A close-up photograph. The leg is involved:
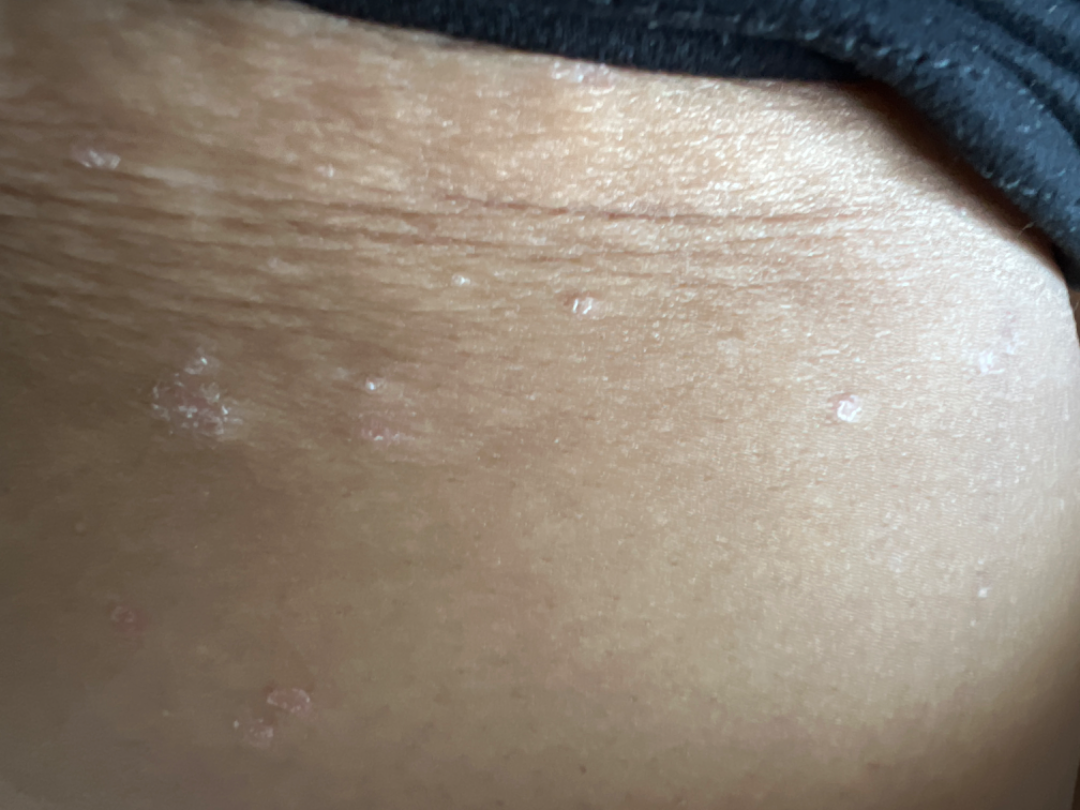dermatologist impression = the leading consideration is Psoriasis.